A close-up photograph. The lesion involves the back of the torso, leg, front of the torso and arm — 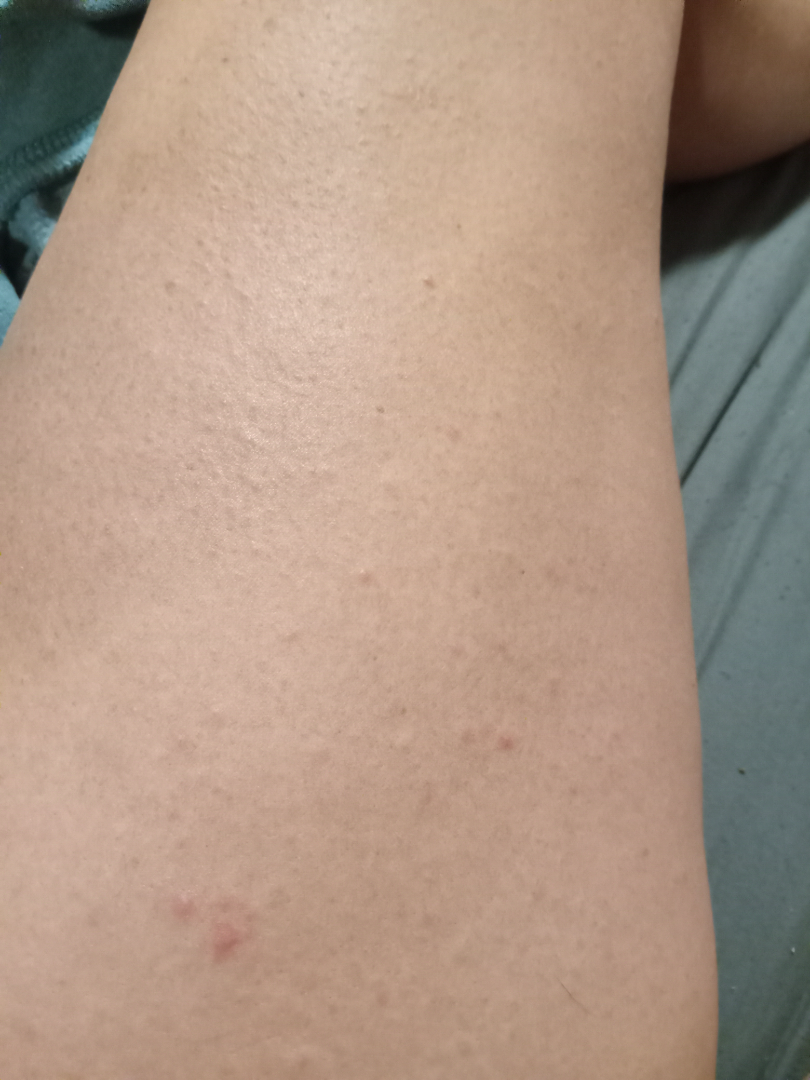assessment — not assessable.